The lesion is described as fluid-filled and raised or bumpy; the photograph is a close-up of the affected area; the patient considered this a rash; the affected area is the leg and top or side of the foot; the lesion is associated with enlargement, itching, pain and burning; reported duration is about one day; the subject is a female aged 60–69.
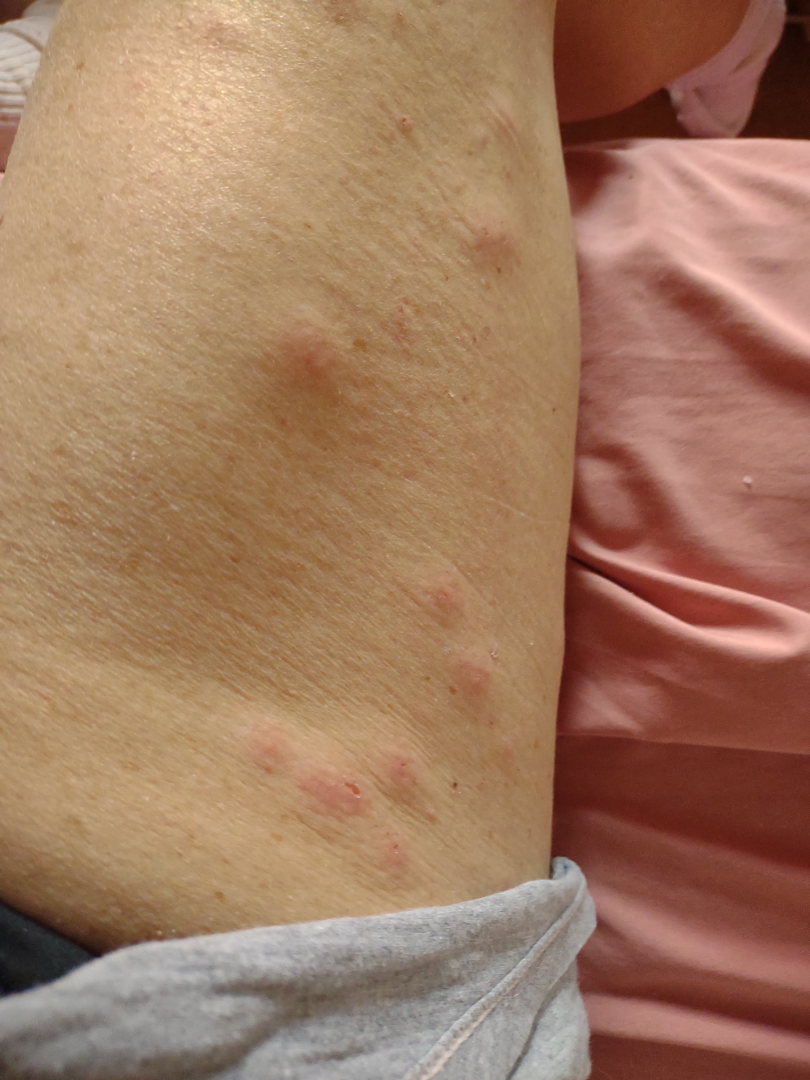Review: Insect Bite (most likely); Deep fungal infection (considered); Abscess (considered).